A dermoscopic image of a skin lesion. By self-report, a personal history of skin cancer and a personal history of cancer. A moderate number of moles by the patient's own estimate. The patient says their skin reddens with sun exposure. A male patient age 77. Collected as part of a research study, without a referral diagnosis.
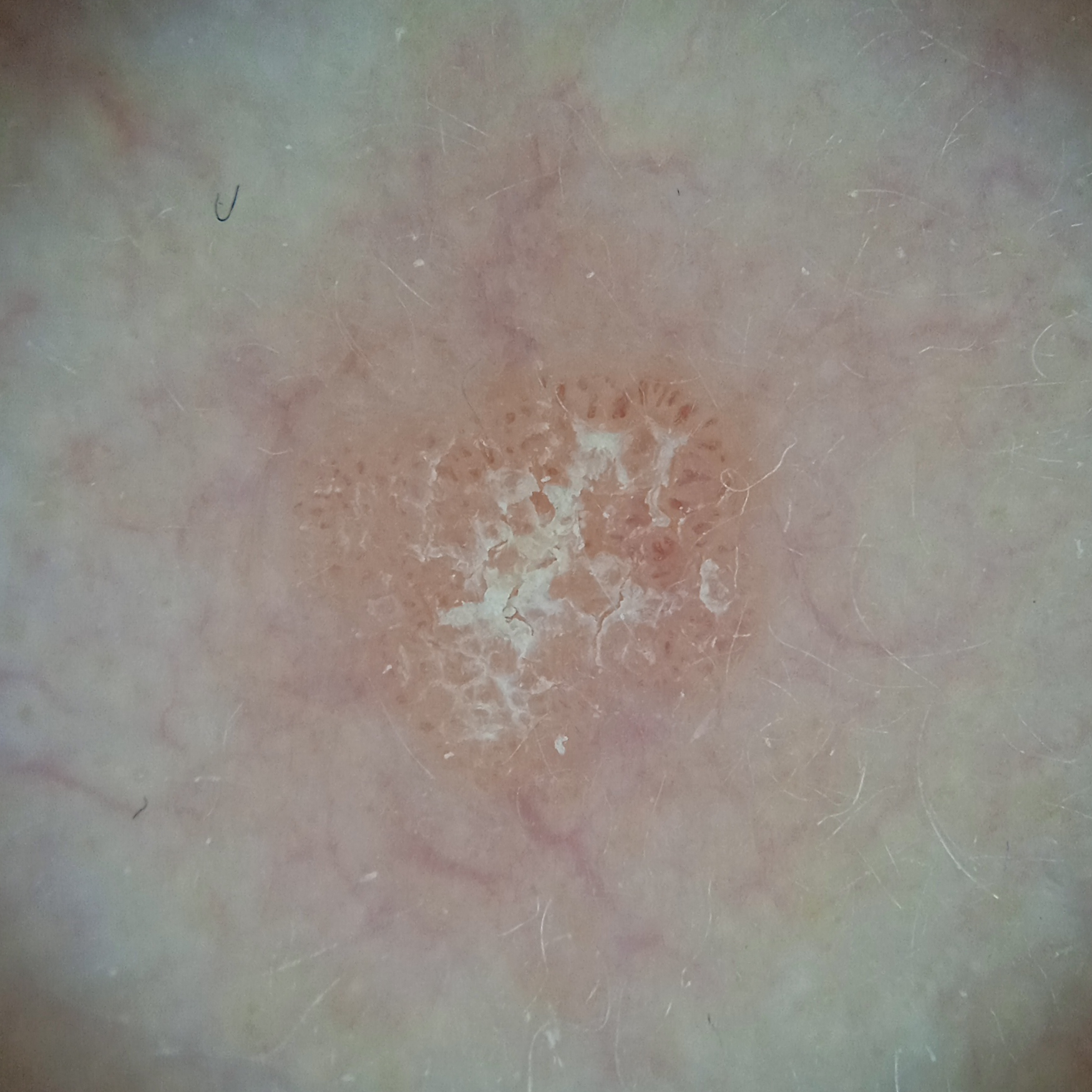location = the face
size = 4.3 mm
diagnostic label = actinic keratosis (dermatologist consensus)